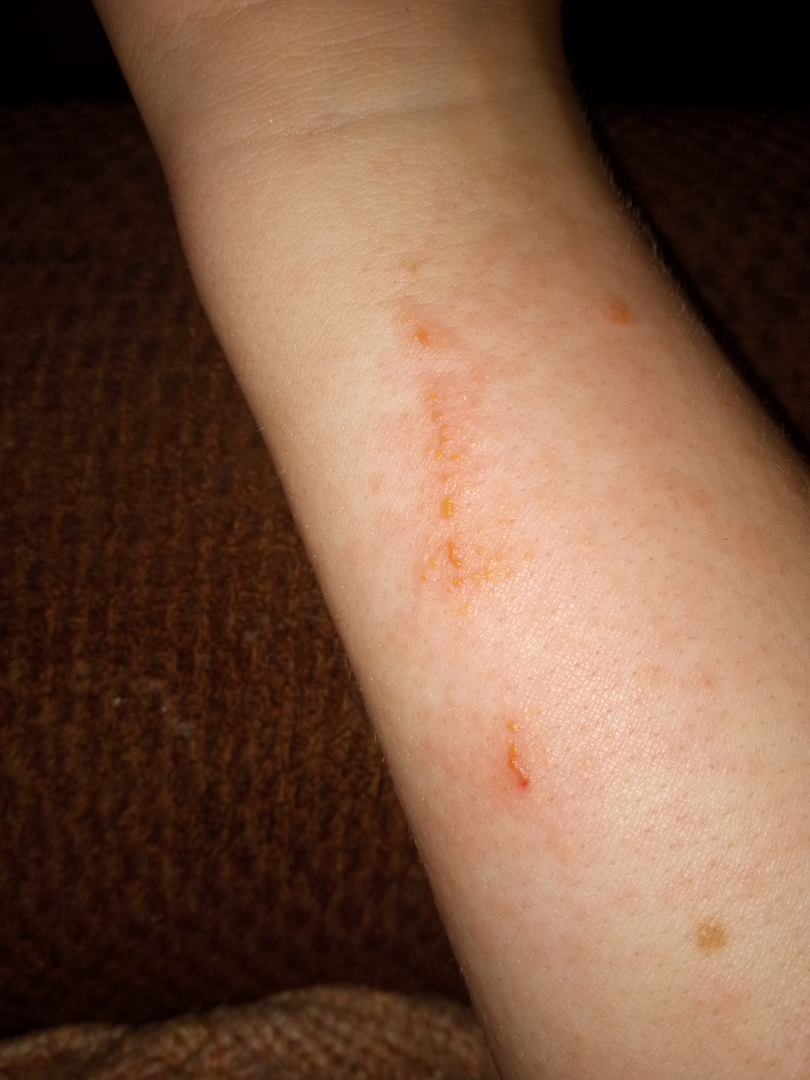{"body_site": "arm", "shot_type": "close-up", "patient": "male", "differential": {"leading": ["Allergic Contact Dermatitis"]}}